The lesion involves the arm · the subject is female · this is a close-up image: 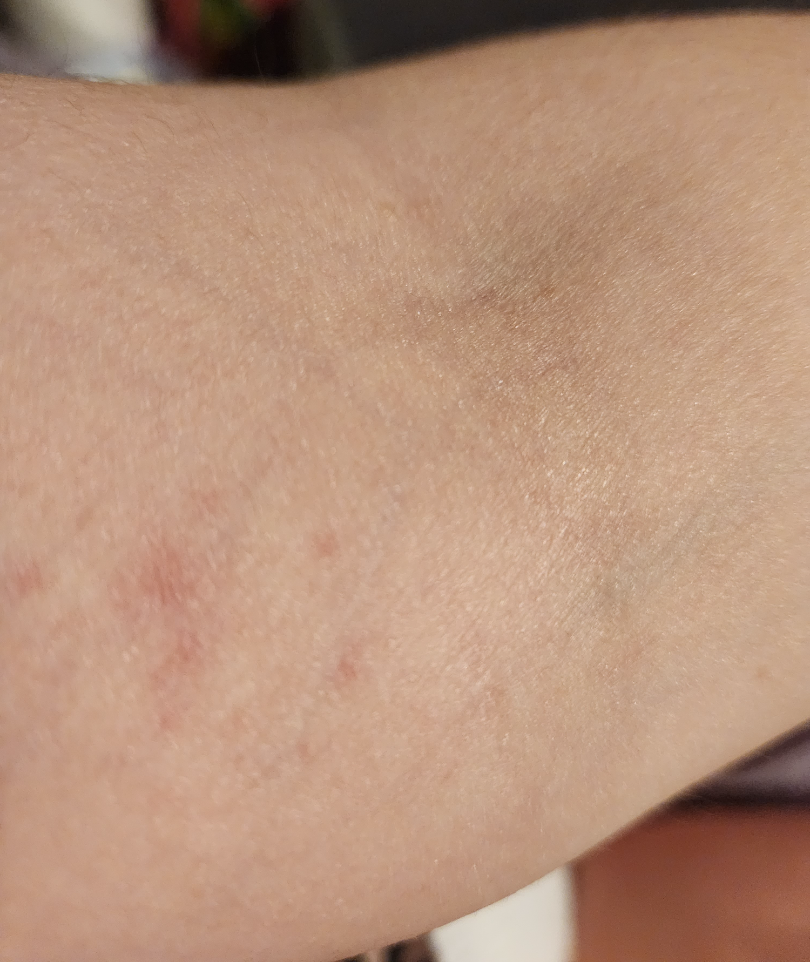Clinical context:
The patient also reports chills, fatigue and joint pain. The lesion is associated with pain, itching and burning. Skin tone: Fitzpatrick IV. Self-categorized by the patient as a rash. The condition has been present for about one day. Texture is reported as raised or bumpy.
Assessment:
The reviewing clinician's impression was: most consistent with Eczema.